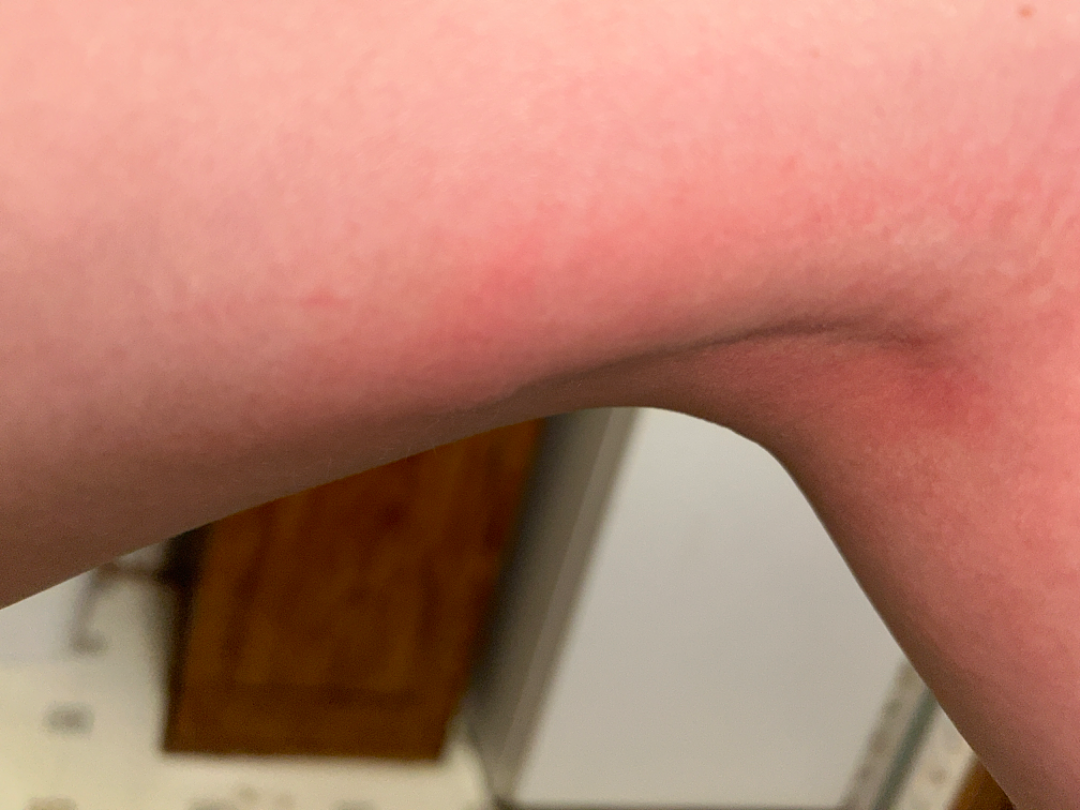Findings:
• skin tone · lay graders estimated Monk Skin Tone 2–3
• site · leg
• symptom duration · less than one week
• framing · at an angle
• diagnostic considerations · one reviewing dermatologist: the differential, in no particular order, includes Allergic Contact Dermatitis and Irritant Contact Dermatitis